Skin tone: human graders estimated MST 2; close-up view:
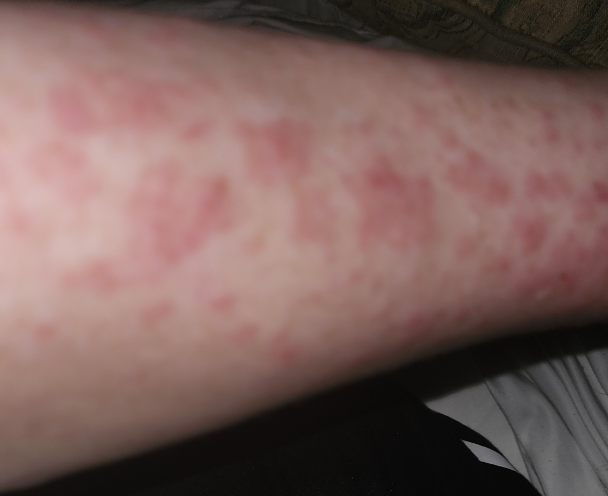Findings:
– assessment · not assessable